The lesion involves the arm, the photograph is a close-up of the affected area:
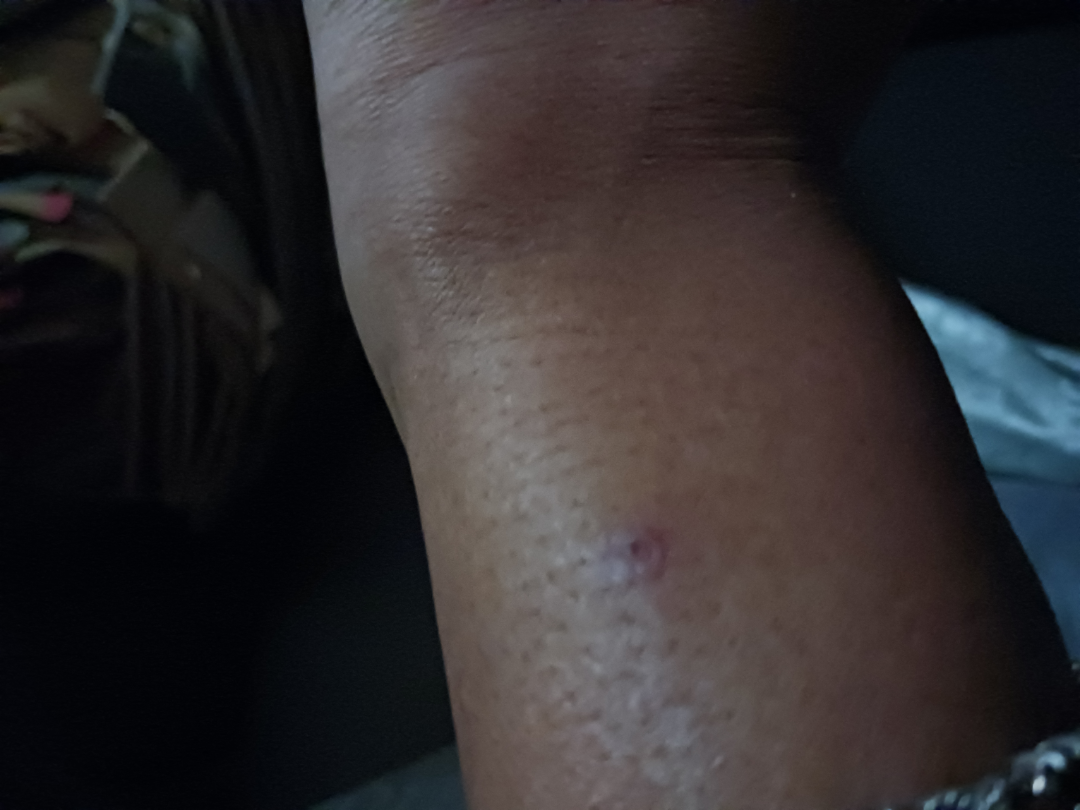The image was not sufficient for the reviewer to characterize the skin condition. Present for one to four weeks. No constitutional symptoms were reported. The patient notes the lesion is raised or bumpy. Symptoms reported: itching.